The lesion involves the leg and arm, the patient is a female aged 40–49, this image was taken at an angle.
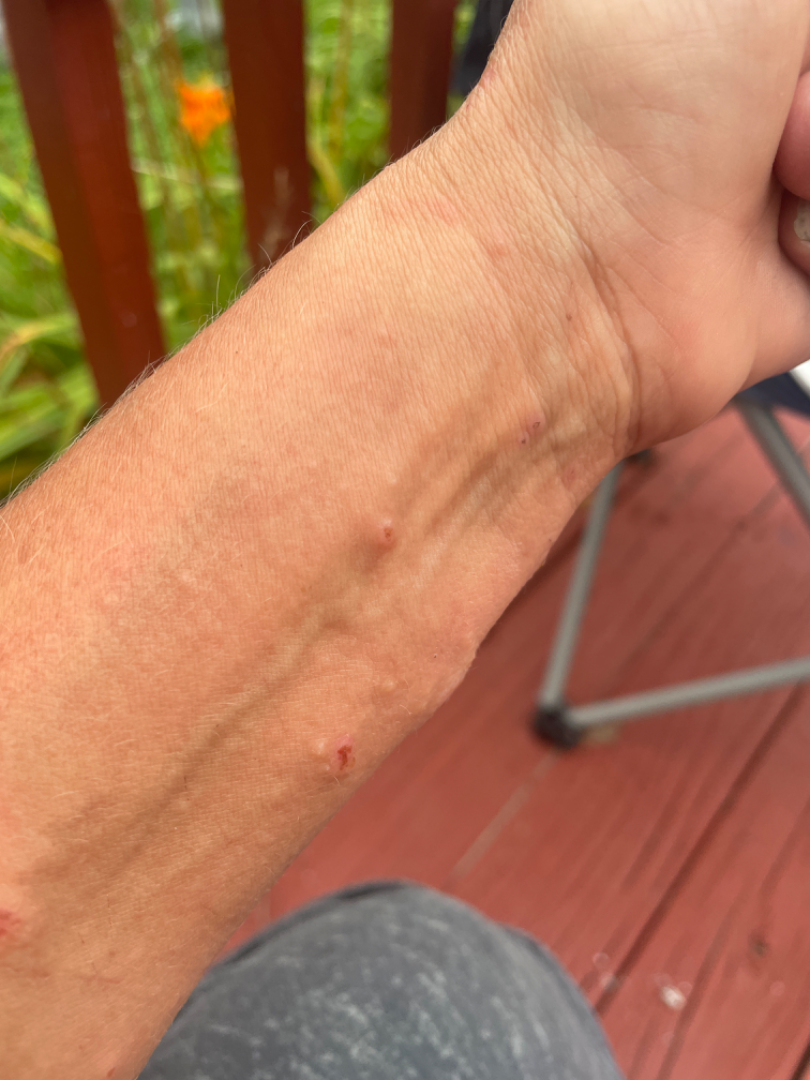The patient described the issue as a rash. Texture is reported as raised or bumpy and fluid-filled. The lesion is associated with enlargement, bothersome appearance, burning and itching. On dermatologist assessment of the image, the leading consideration is Allergic Contact Dermatitis; the differential also includes Contact dermatitis; less likely is Herpes Zoster.